Texture is reported as fluid-filled and raised or bumpy · self-categorized by the patient as a rash · no constitutional symptoms were reported · the contributor notes enlargement, bleeding, pain, itching and bothersome appearance · located on the top or side of the foot · an image taken at an angle — 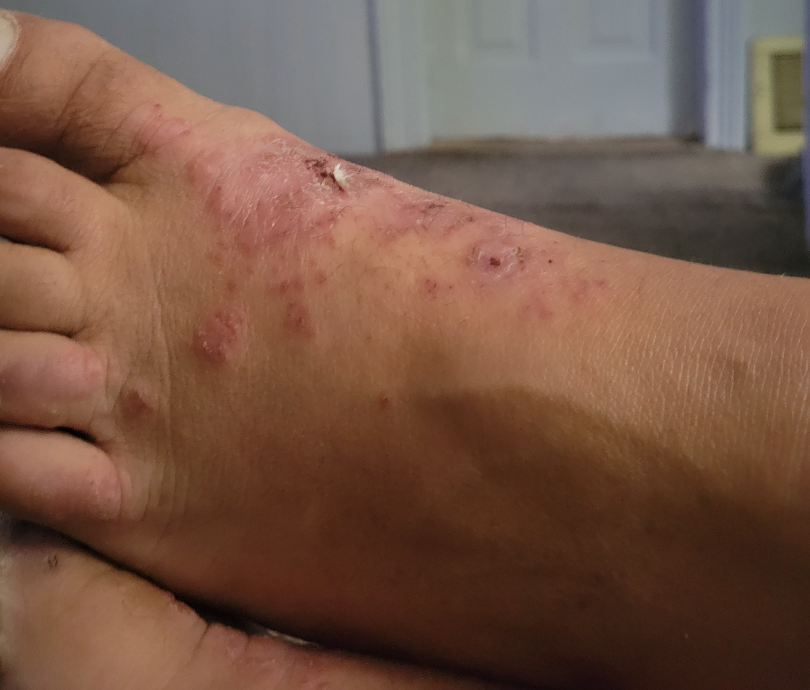Assessment: On photographic review, the primary impression is Tinea; also consider Eczema; also raised was Psoriasis.